A contact-polarized dermoscopy image of a skin lesion · the patient is Fitzpatrick I · a female subject in their mid- to late 60s — 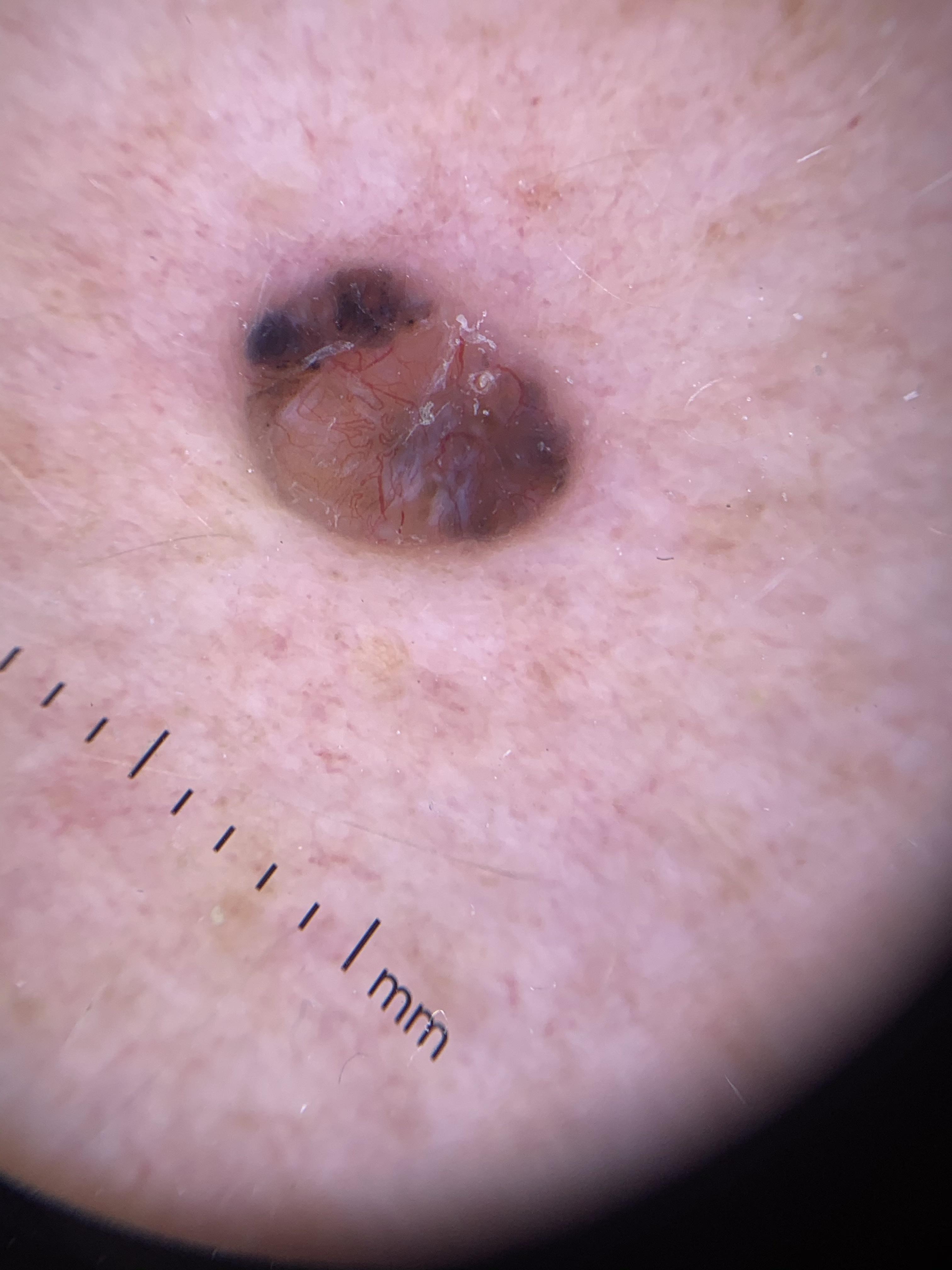* body site · an upper extremity
* diagnostic label · Basal cell carcinoma (biopsy-proven)